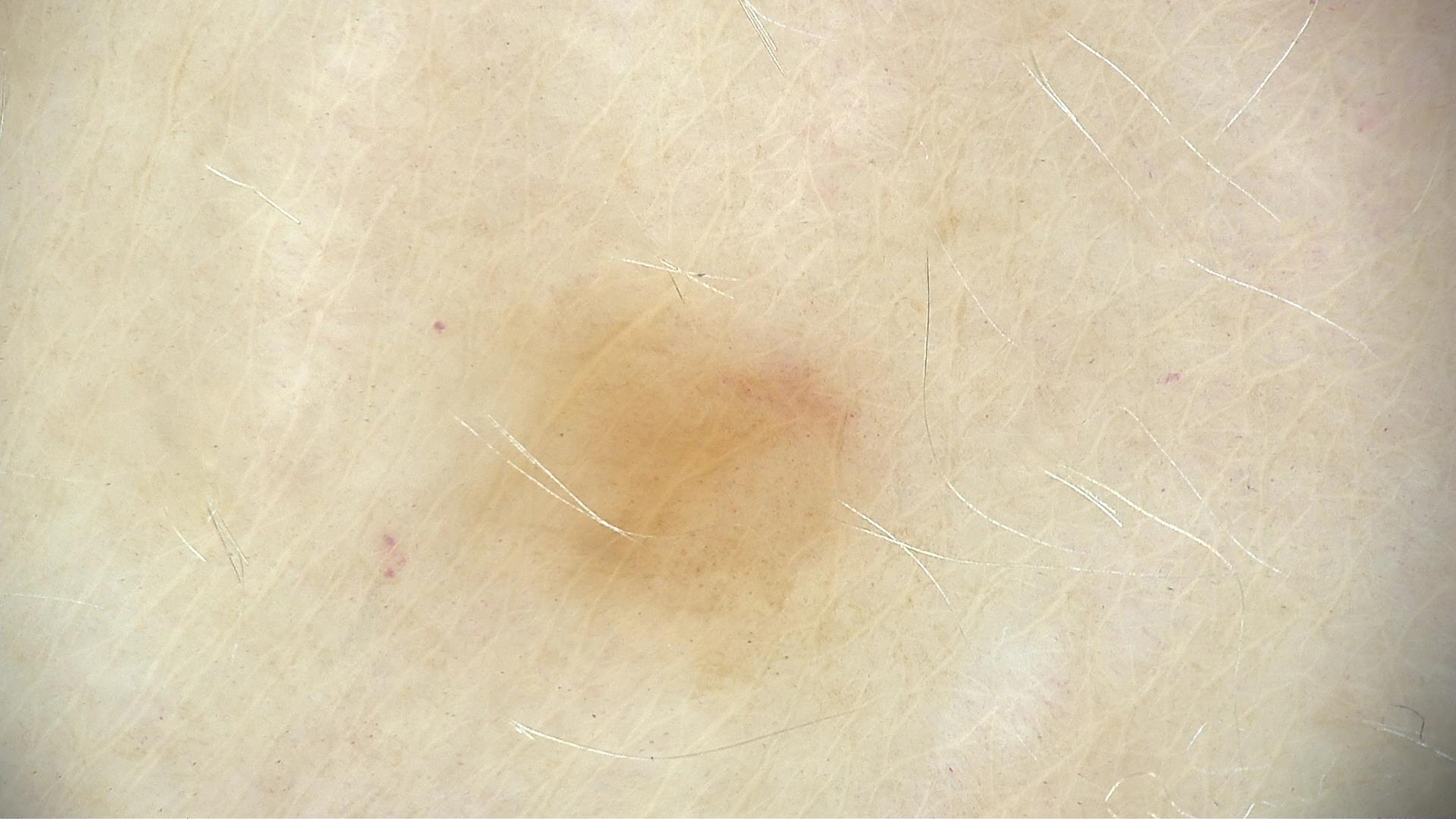Q: What is the imaging modality?
A: dermatoscopy
Q: What is this lesion?
A: junctional nevus (expert consensus)